The photograph is a close-up of the affected area; no constitutional symptoms were reported; self-categorized by the patient as a rash; the lesion is described as raised or bumpy and rough or flaky; present for one to three months; the lesion involves the arm; the patient indicates enlargement, itching, darkening and bothersome appearance; male subject, age 18–29: 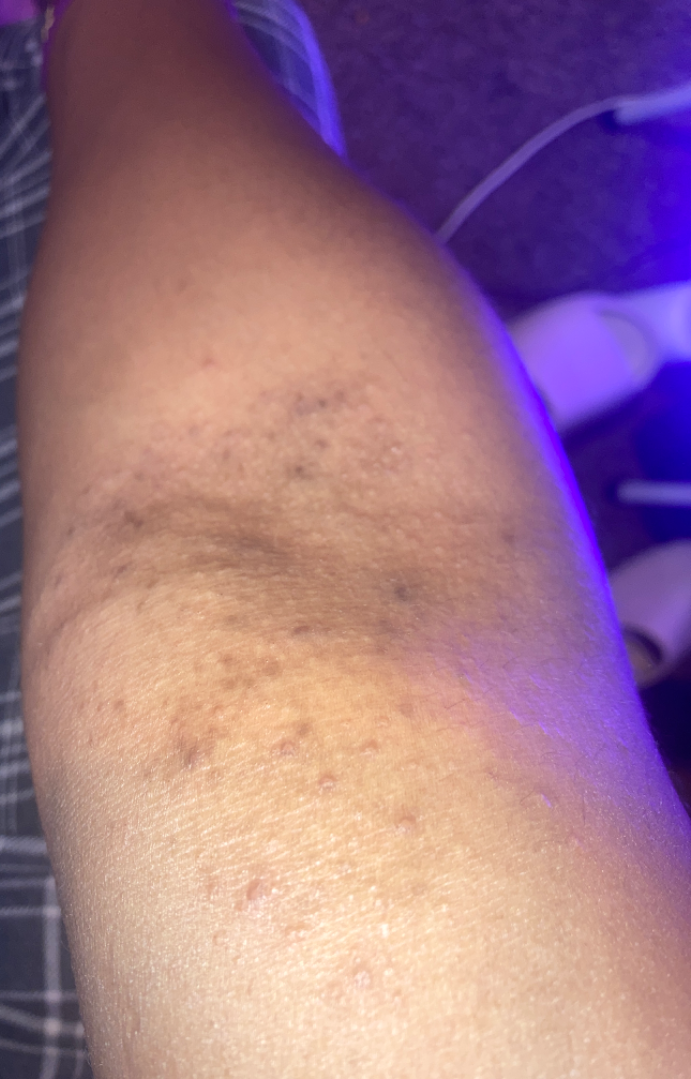Q: What conditions are considered?
A: one reviewing dermatologist: consistent with Eczema